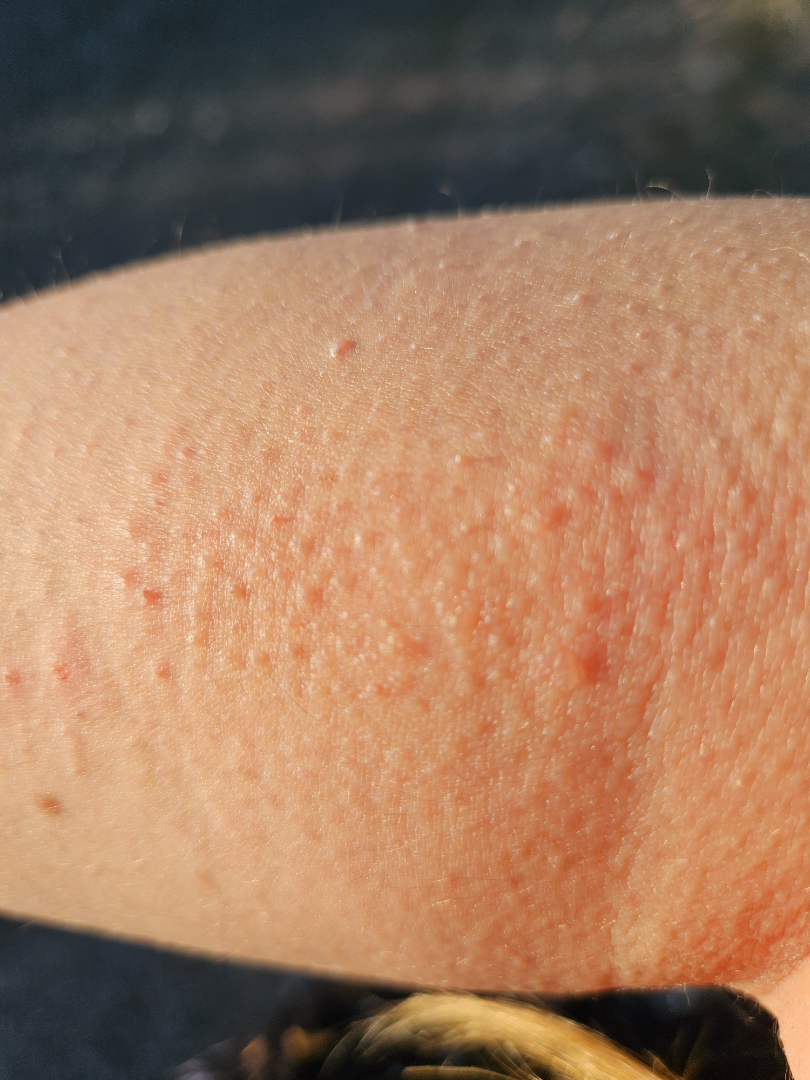clinical impression: the differential includes Keratosis pilaris, Eczema and Allergic Contact Dermatitis, with no clear leading consideration.